A dermoscopic close-up of a skin lesion.
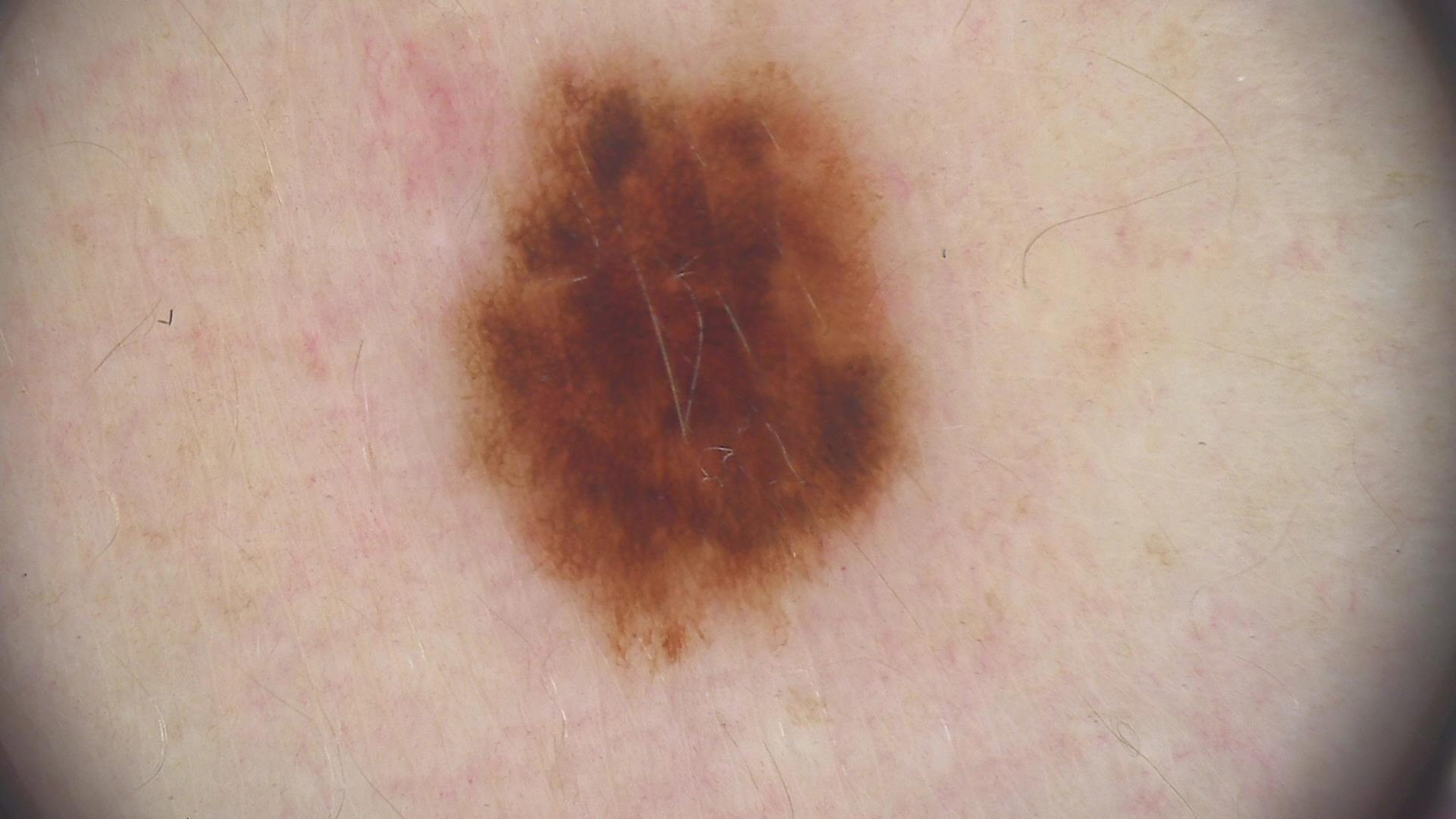The diagnosis was a benign lesion — a dysplastic junctional nevus.